Dermoscopy of a skin lesion.
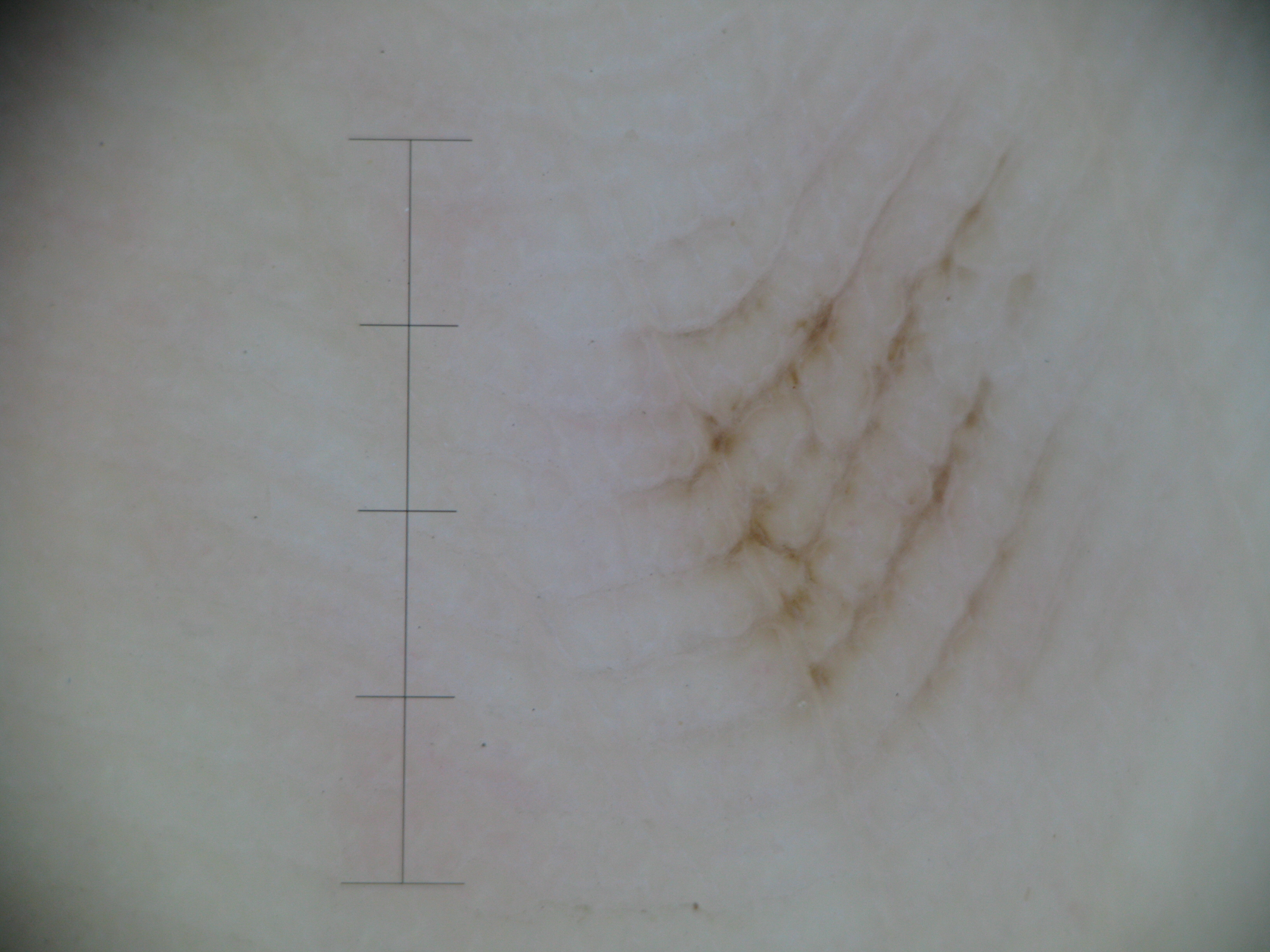The diagnosis was a banal lesion — an acral junctional nevus.